Skin tone: Fitzpatrick IV. The patient indicates associated joint pain. The lesion is associated with bothersome appearance. The lesion is described as raised or bumpy. A close-up photograph. Reported duration is one to four weeks. The patient described the issue as a hair problem. Located on the head or neck:
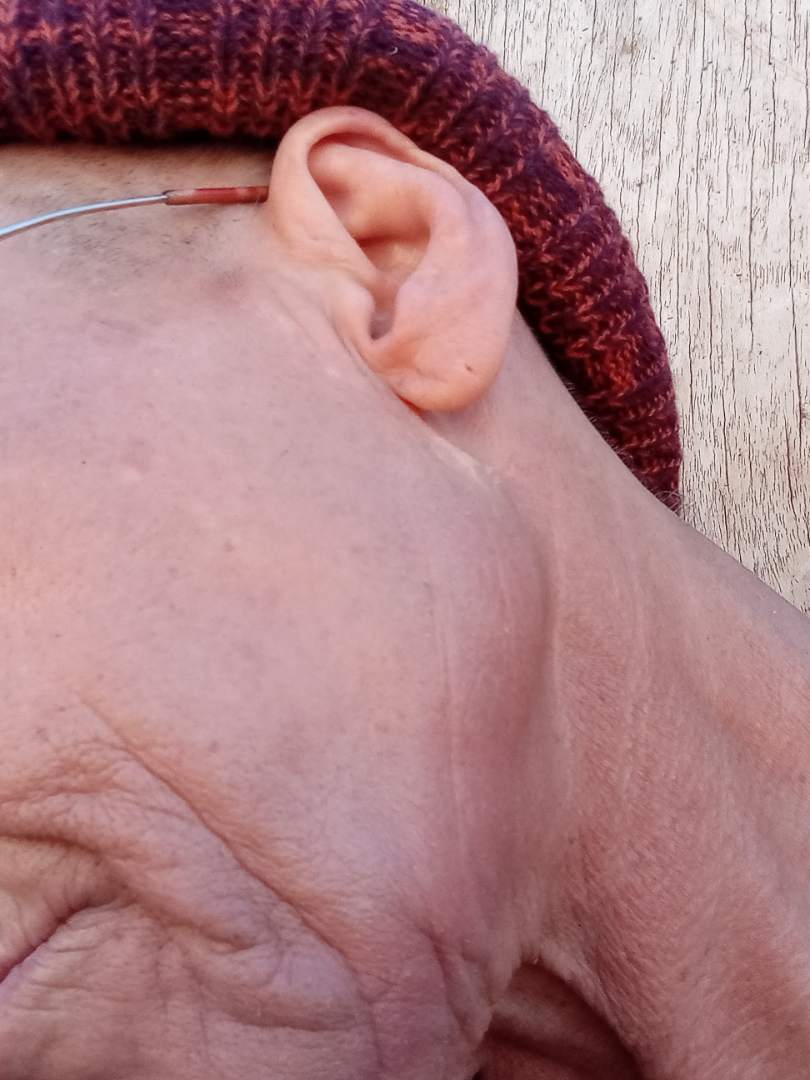Assessment:
The reviewing dermatologist did not identify a discernible skin condition.